A dermoscopy image of a single skin lesion: 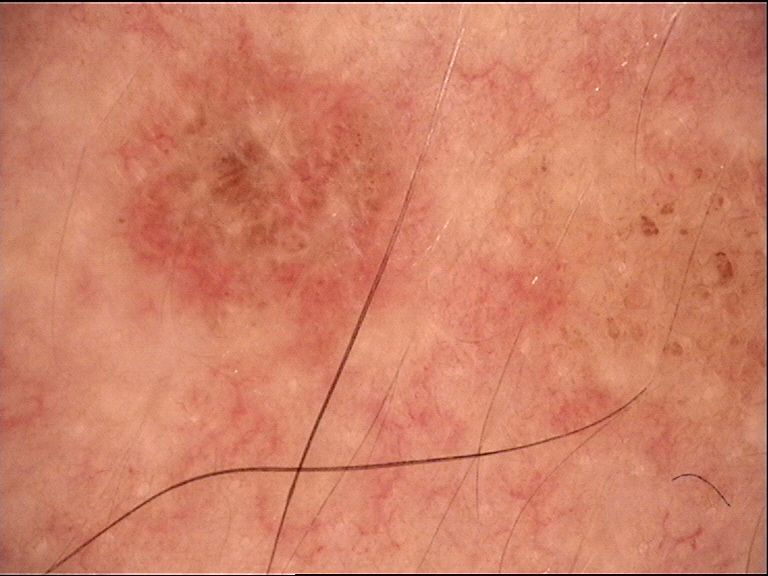label: dermal nevus (expert consensus).